A dermoscopic view of a skin lesion.
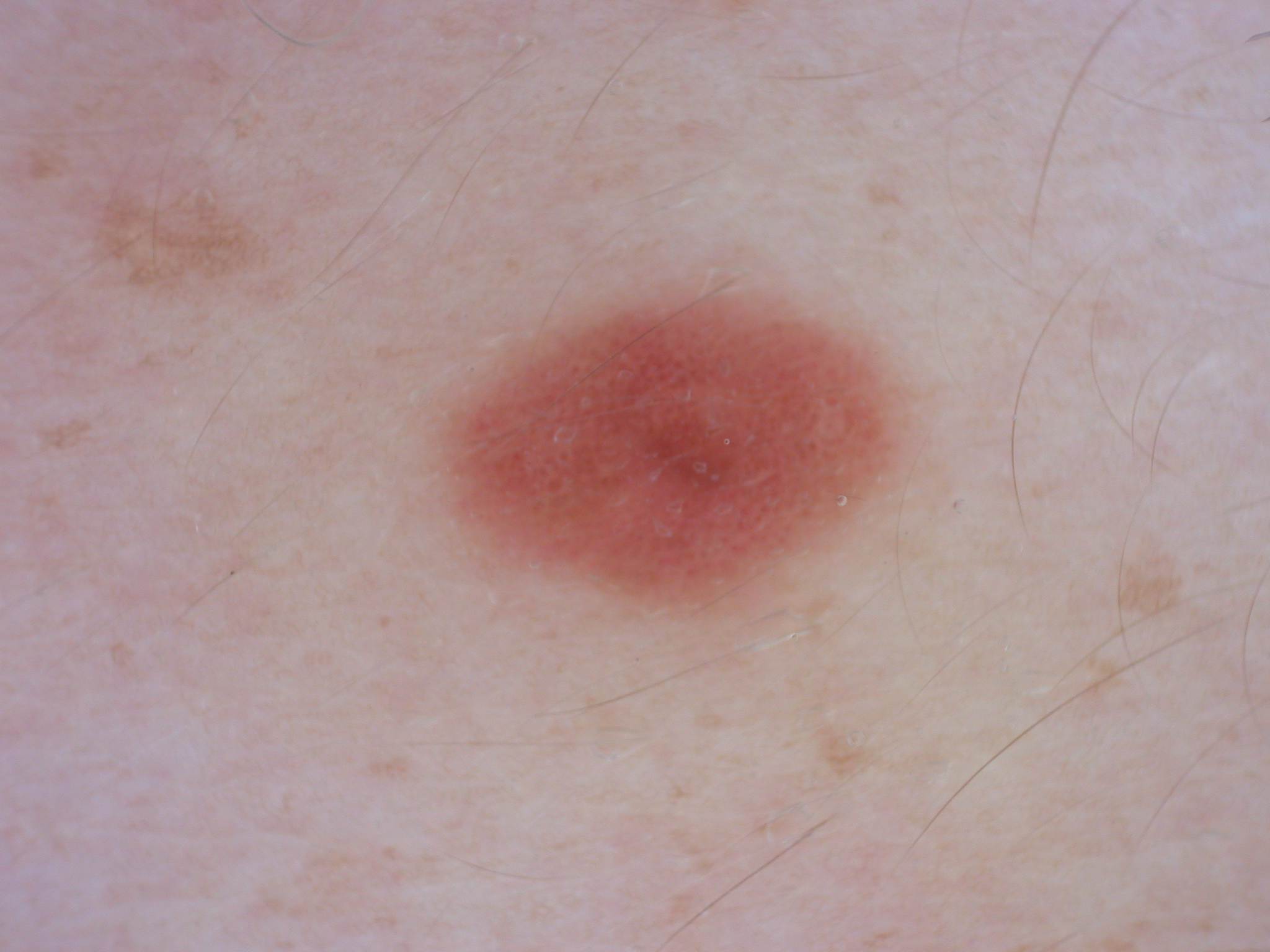Case summary:
The lesion's extent is 442/293/897/614.
Impression:
The lesion was assessed as a melanocytic nevus, a benign lesion.